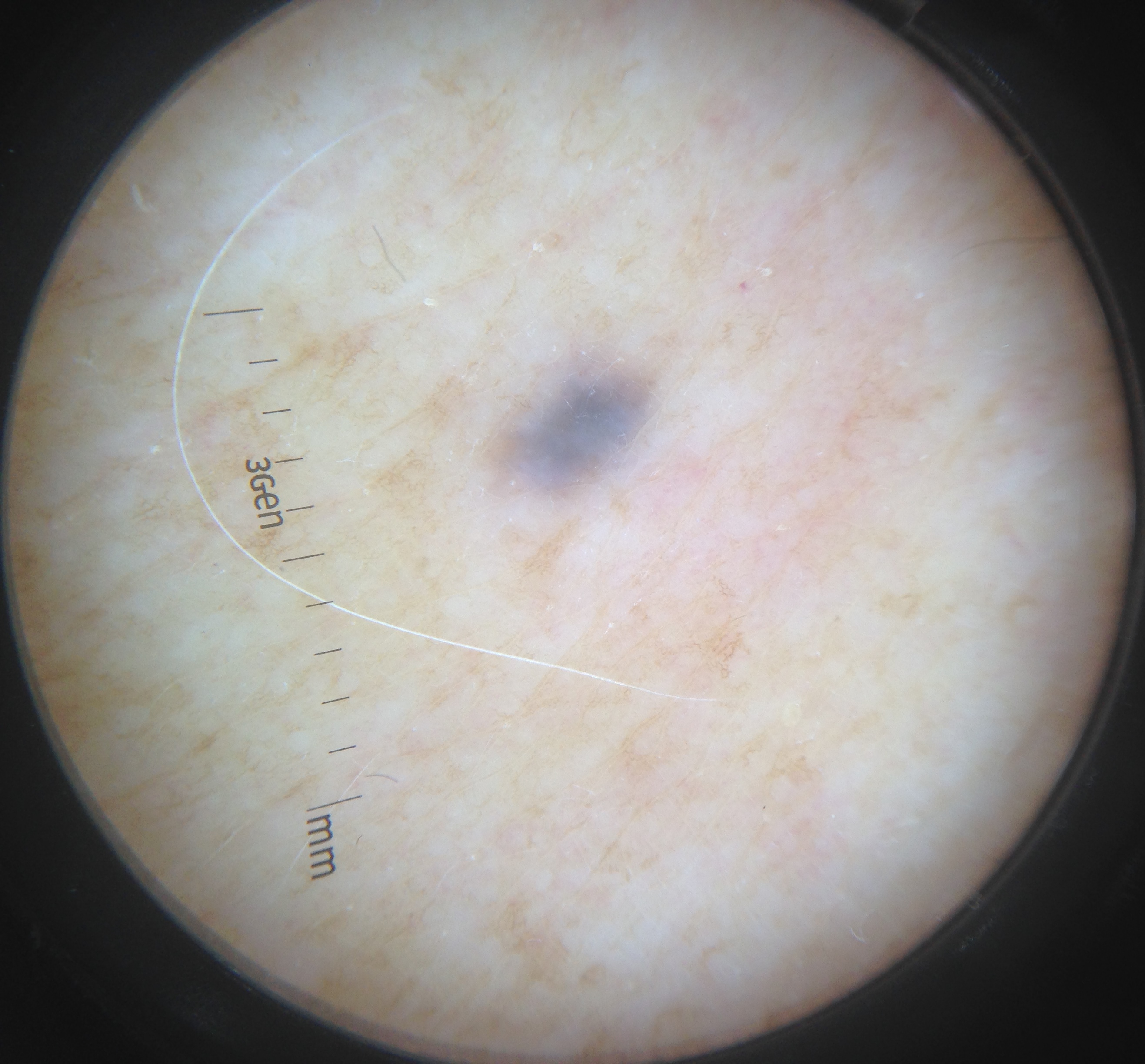image type = dermatoscopy
diagnostic label = blue nevus (expert consensus)